The lesion involves the top or side of the foot; the contributor is a female aged 40–49; the photograph is a close-up of the affected area; no relevant lesion symptoms reported; texture is reported as raised or bumpy.
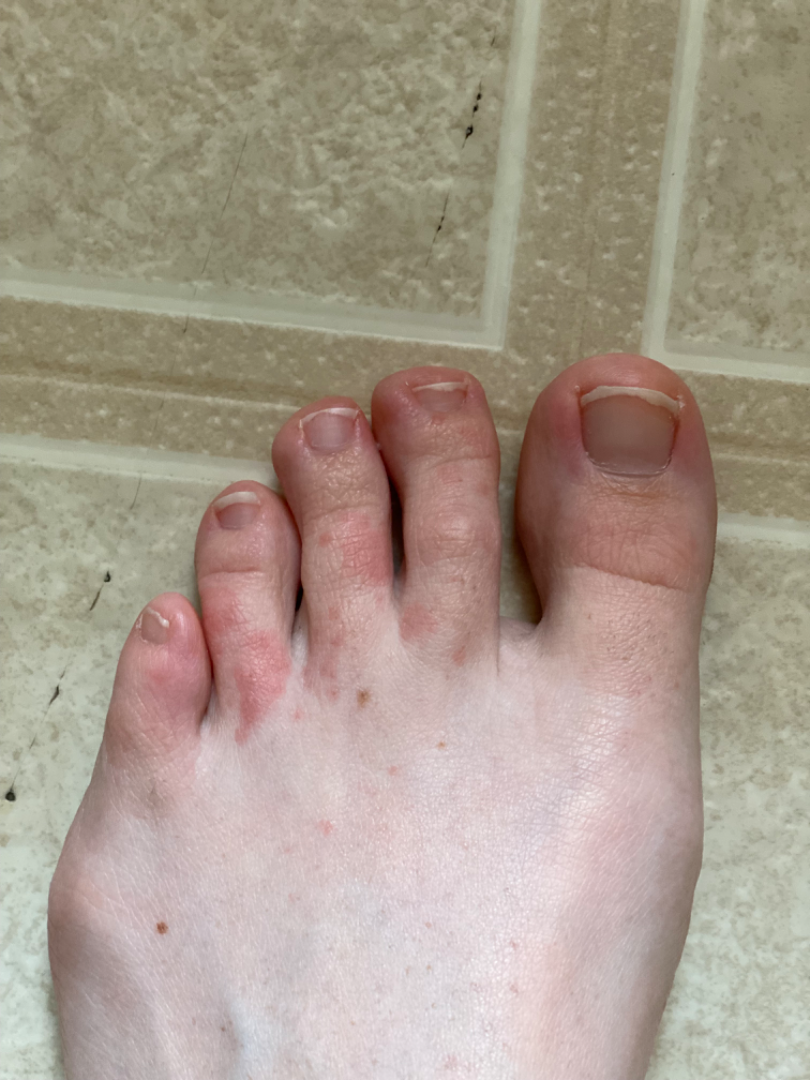<dermatology_case>
<assessment>could not be assessed</assessment>
</dermatology_case>